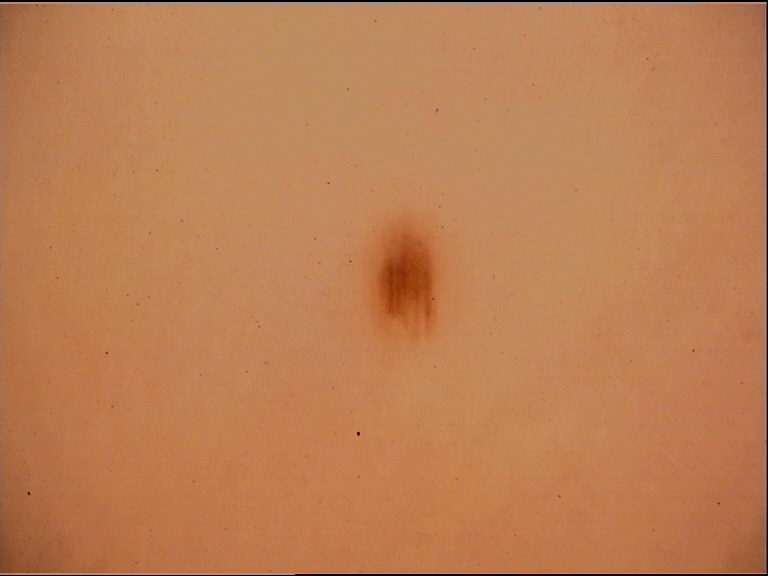image type: dermatoscopy
classification: banal
class: acral junctional nevus (expert consensus)